Texture is reported as flat and raised or bumpy. The patient is 50–59, female. This image was taken at a distance. The back of the hand, back of the torso, front of the torso and arm are involved. Self-categorized by the patient as a rash. The patient indicates associated fatigue and joint pain. Symptoms reported: enlargement, burning, itching and bothersome appearance. The patient indicates the condition has been present for less than one week:
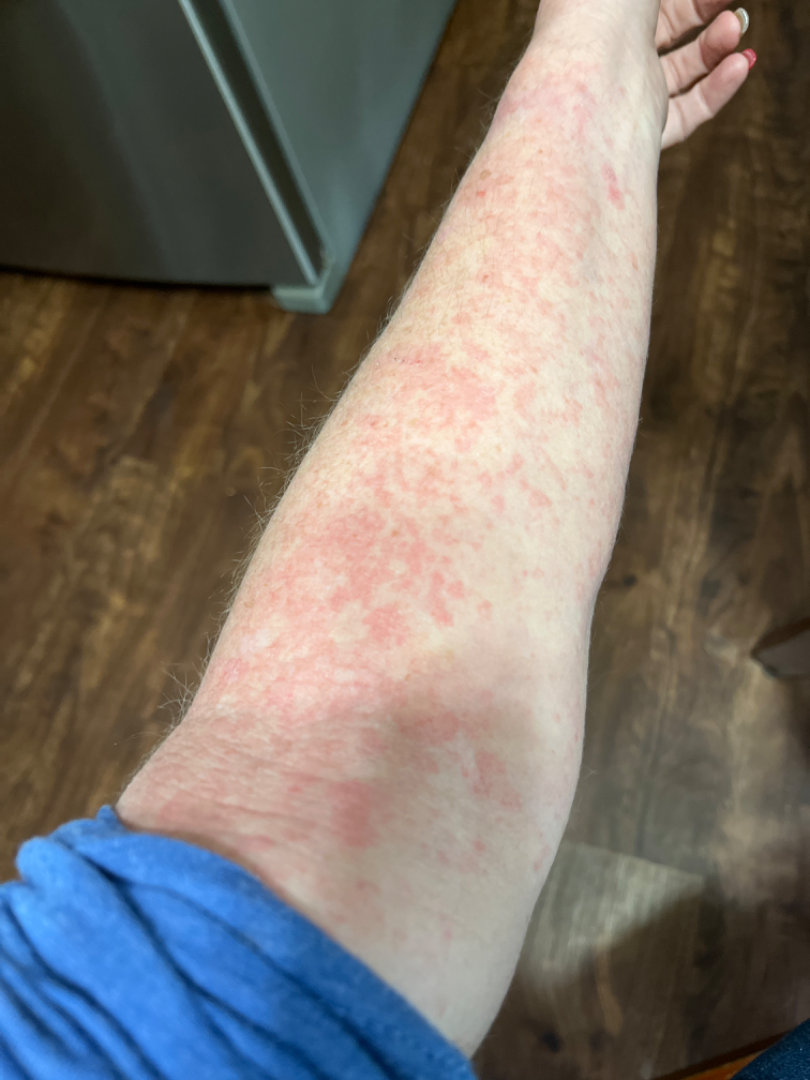{"differential": {"tied_lead": ["Drug Rash", "Urticaria"]}}